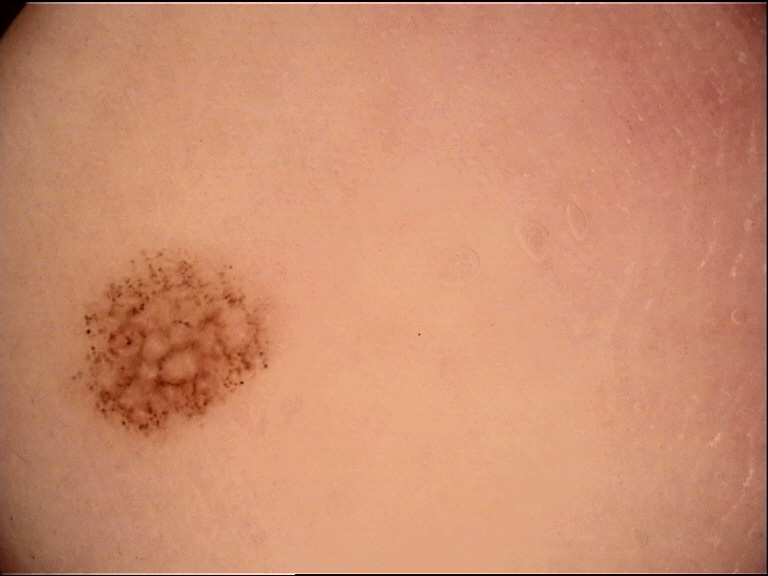Case:
- modality: dermoscopy
- class: acral dysplastic junctional nevus (expert consensus)